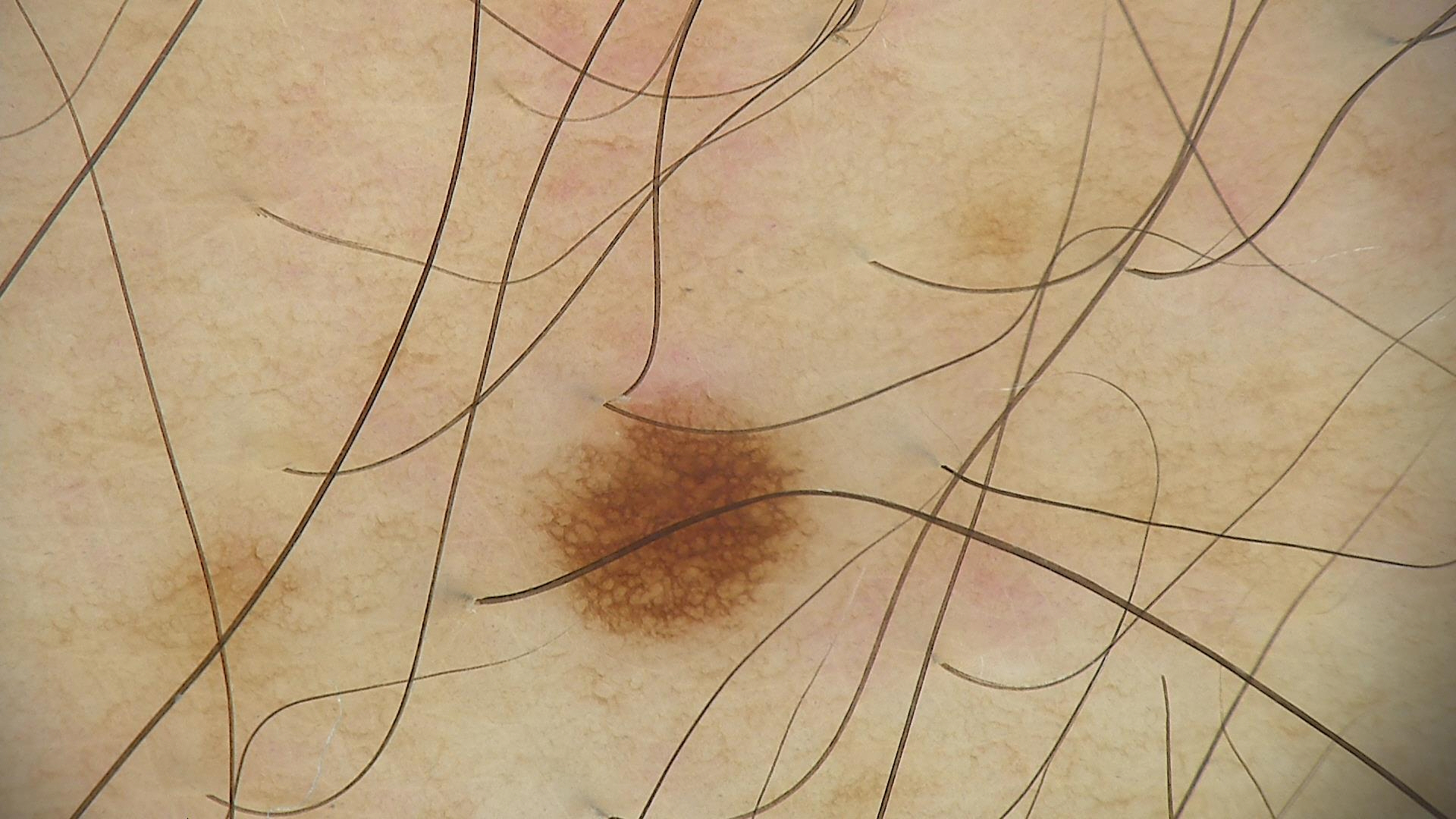imaging — dermoscopy | diagnostic label — dysplastic junctional nevus (expert consensus).